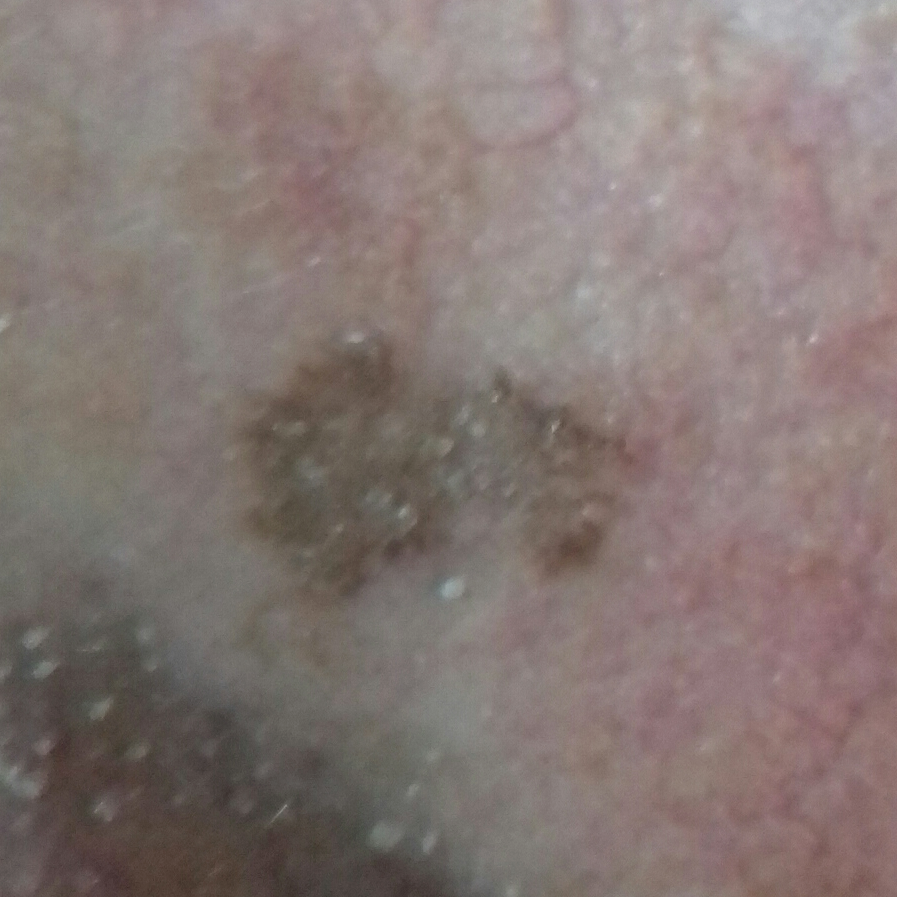A clinical photo of a skin lesion taken with a smartphone. A patient aged 75. The lesion involves the nose. By the patient's account, the lesion has grown, but is not elevated and has not bled. Expert review favored a seborrheic keratosis.